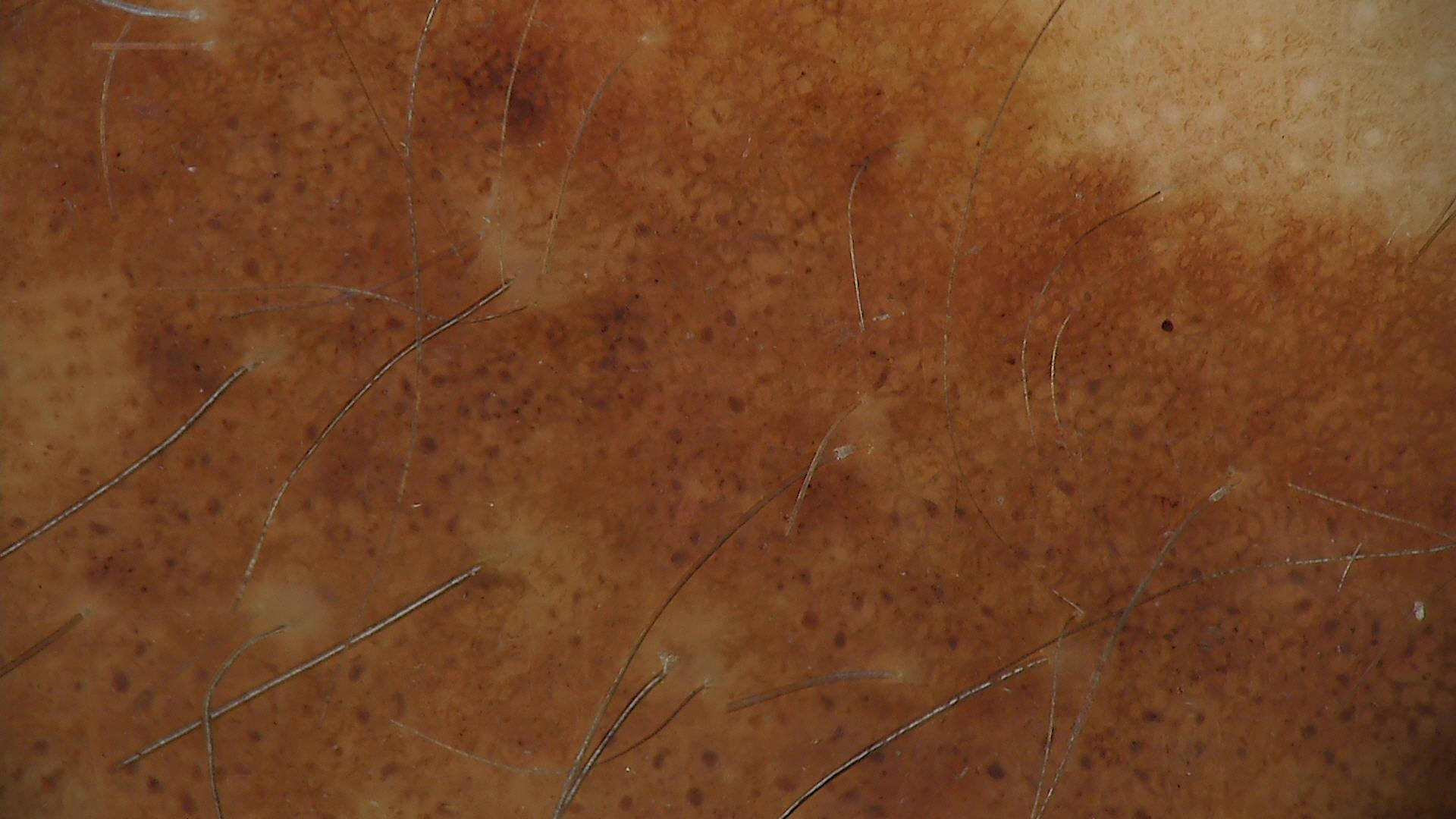The morphology is that of a banal lesion. The diagnostic label was a congenital junctional nevus.